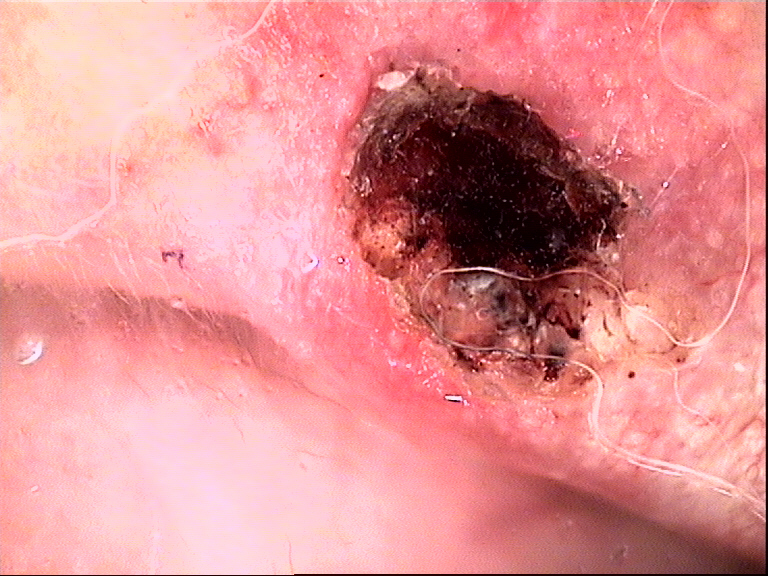Confirmed on histopathology as a keratinocytic lesion — a squamous cell carcinoma.